The patient considered this a rash, the back of the hand is involved, the patient reports itching, this is a close-up image, the patient reports the condition has been present for less than one week, the lesion is described as raised or bumpy — 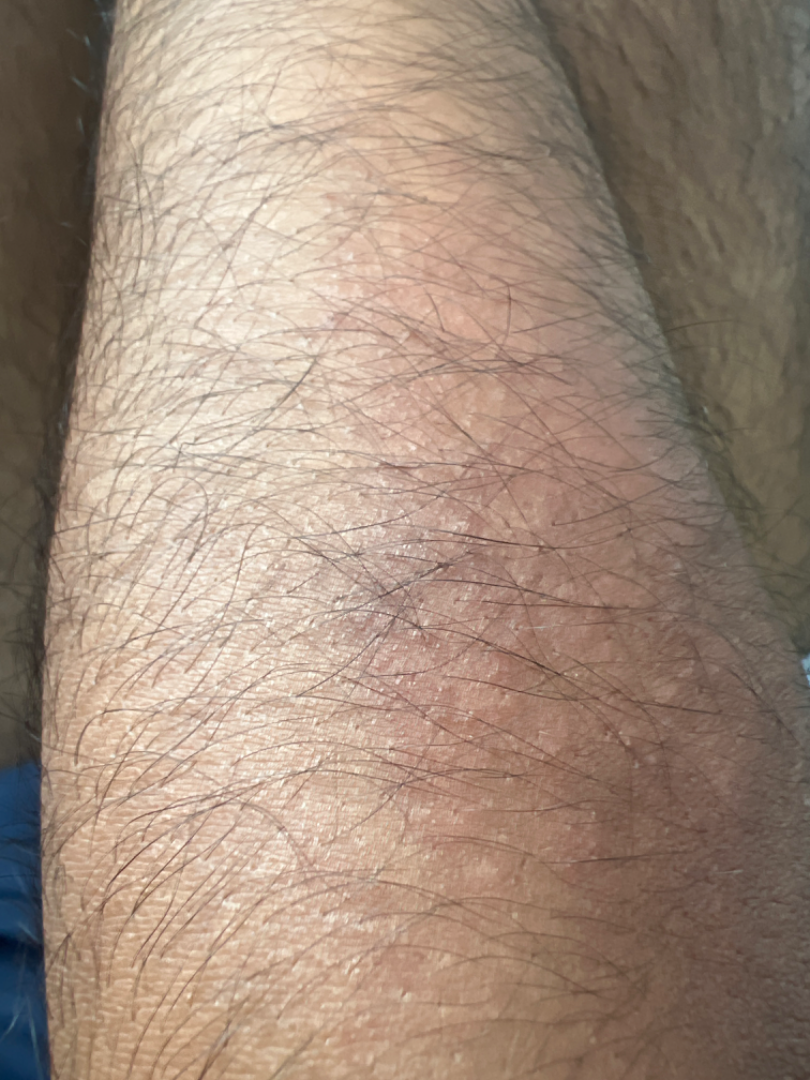A single dermatologist reviewed the case: the primary impression is Eczema; with consideration of Xerosis.